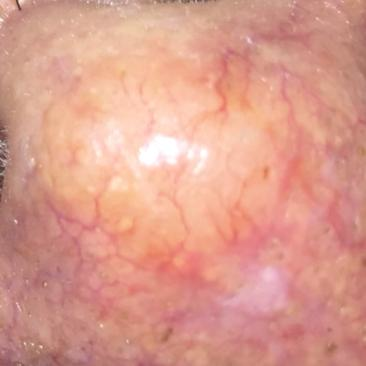Recorded as Fitzpatrick skin type II. A male patient 44 years old. The lesion is located on the nose. The lesion measures 10 × 10 mm. By the patient's account, the lesion itches, has grown, and is elevated. Biopsy-confirmed as a basal cell carcinoma.